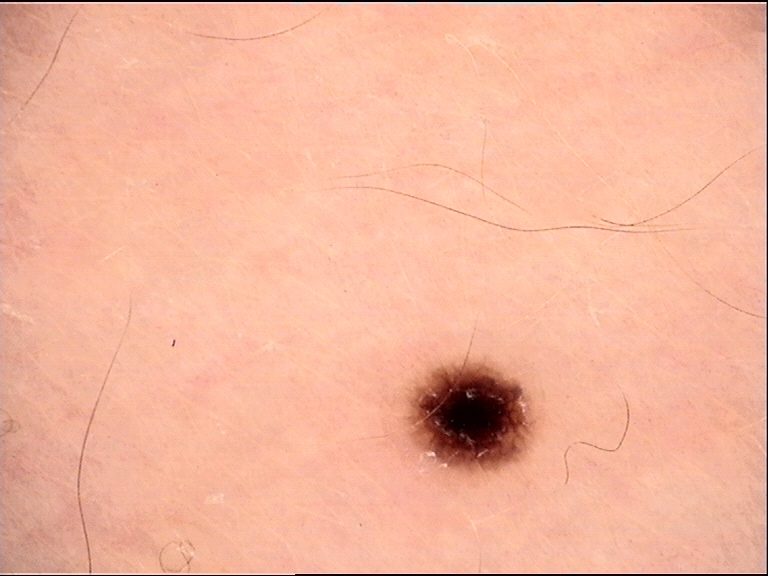Consistent with a benign lesion — a dysplastic junctional nevus.